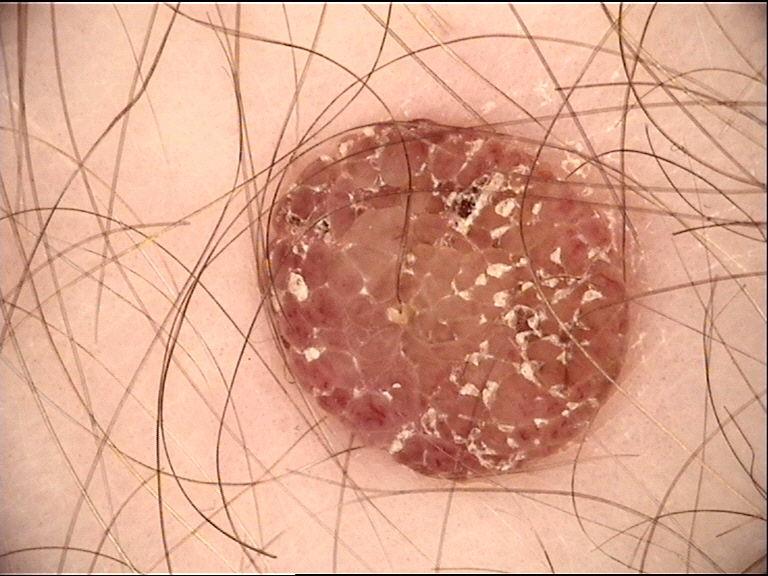classification: banal
class: dermal nevus (expert consensus)